Located on the front of the torso. Female contributor, age 18–29. An image taken at a distance: 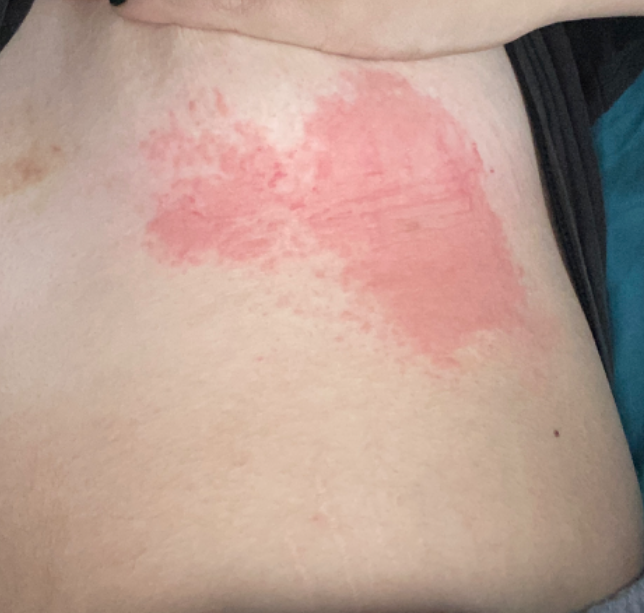Notes:
– skin tone — Fitzpatrick III
– present for — less than one week
– other reported symptoms — none reported
– patient-reported symptoms — itching, bothersome appearance, enlargement, darkening and burning
– self-categorized as — skin that appeared healthy to them
– differential diagnosis — three dermatologists independently reviewed the case: most consistent with Allergic Contact Dermatitis; a remote consideration is Acute dermatitis, NOS; less likely is Cellulitis; less probable is Tinea; lower on the differential is Eczema; a more distant consideration is Urticarial vasculitis